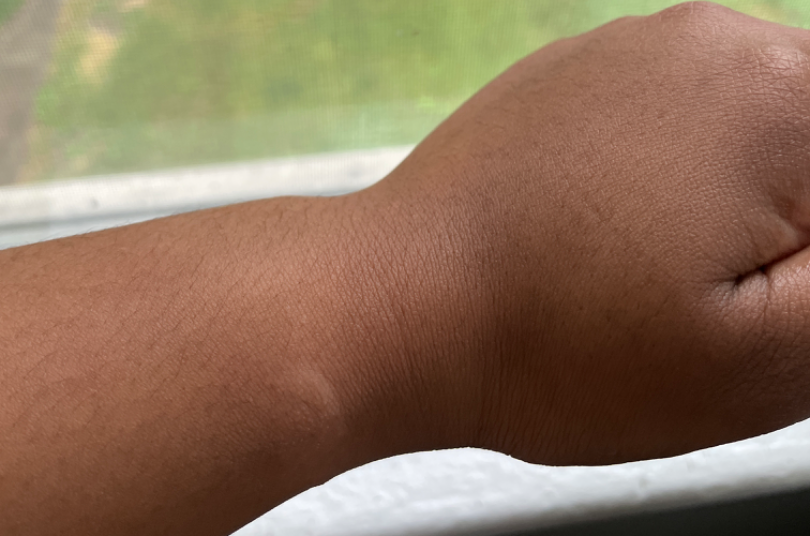Female patient, age 30–39. An image taken at an angle. Located on the arm. Three independent reviewers: the differential is split between Contact dermatitis, Eczema and Acute and chronic dermatitis; less probable is Allergic Contact Dermatitis.